The photograph was taken at an angle.
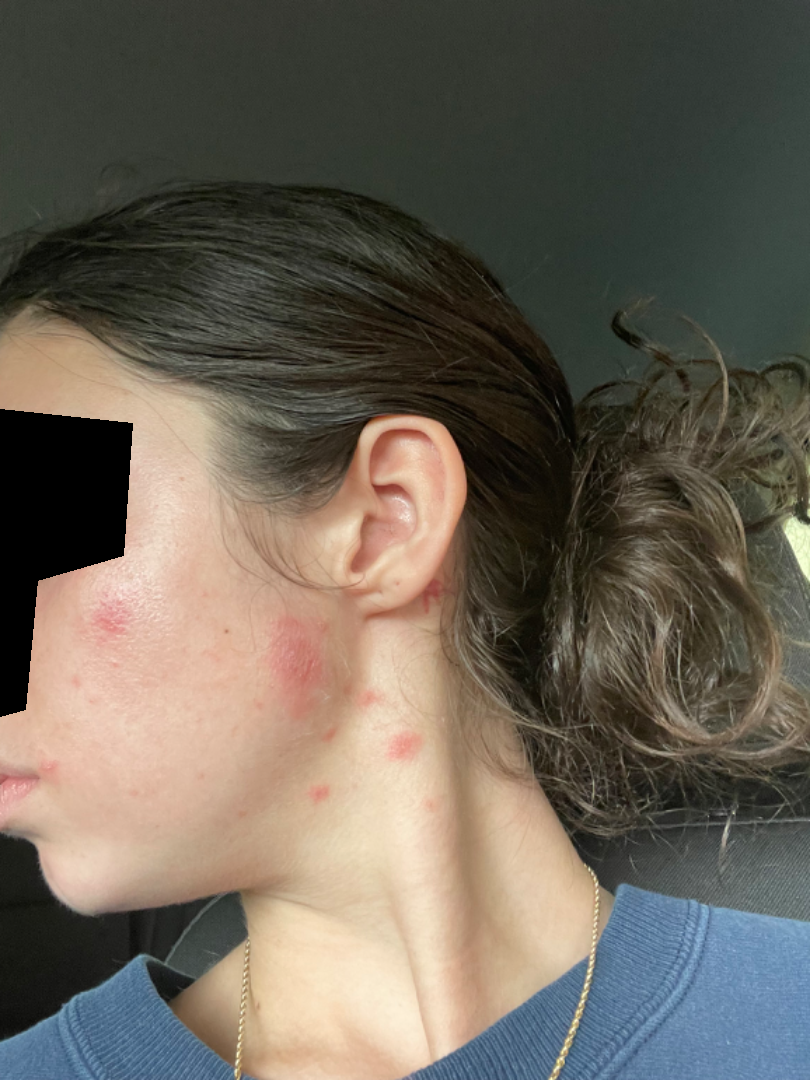Case summary:
- diagnostic considerations — most likely Acne; possibly Impetigo